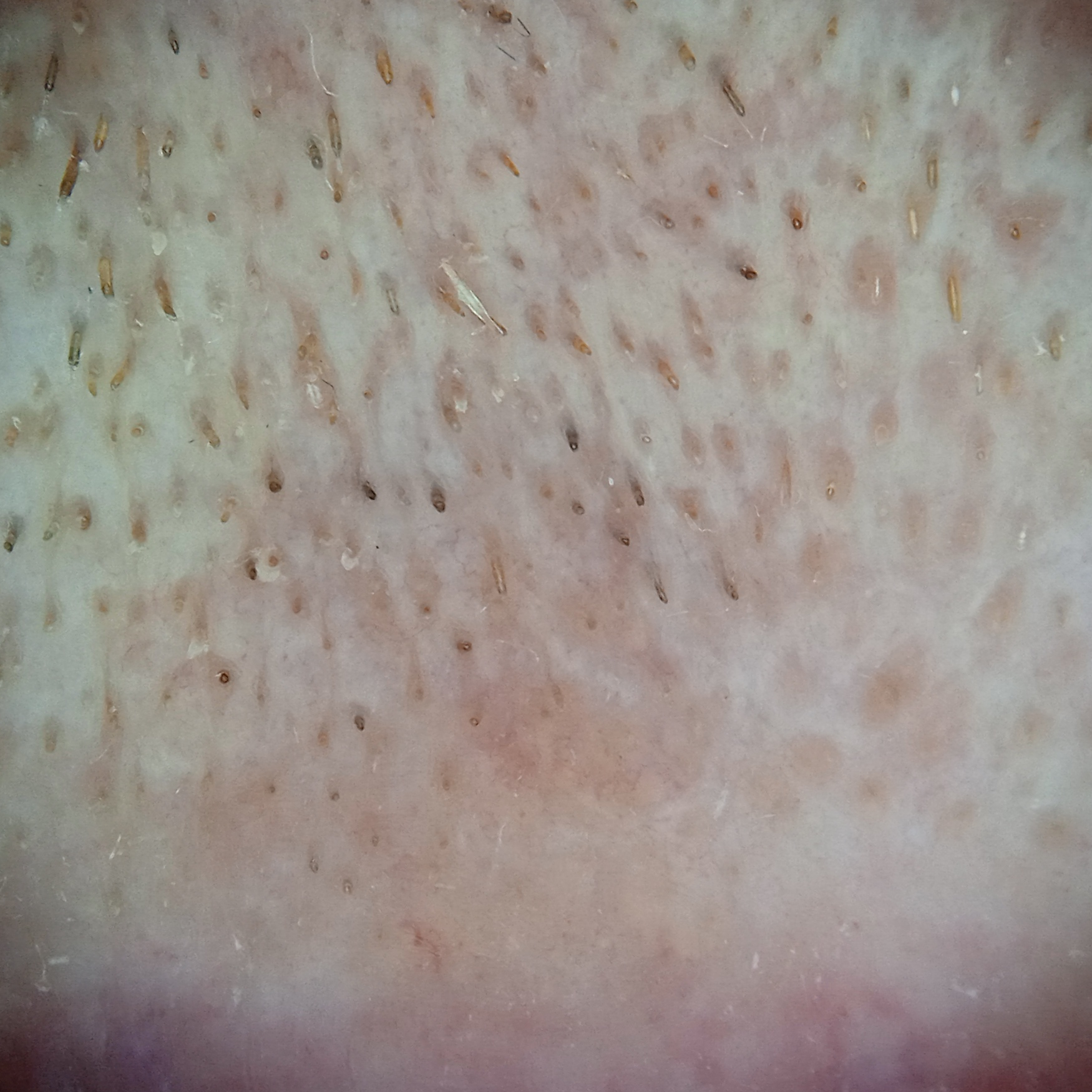Case:
– imaging: dermoscopy
– patient: male, 77 years of age
– referral context: research study (no referral diagnosis)
– diagnostic label: actinic keratosis (dermatologist consensus)